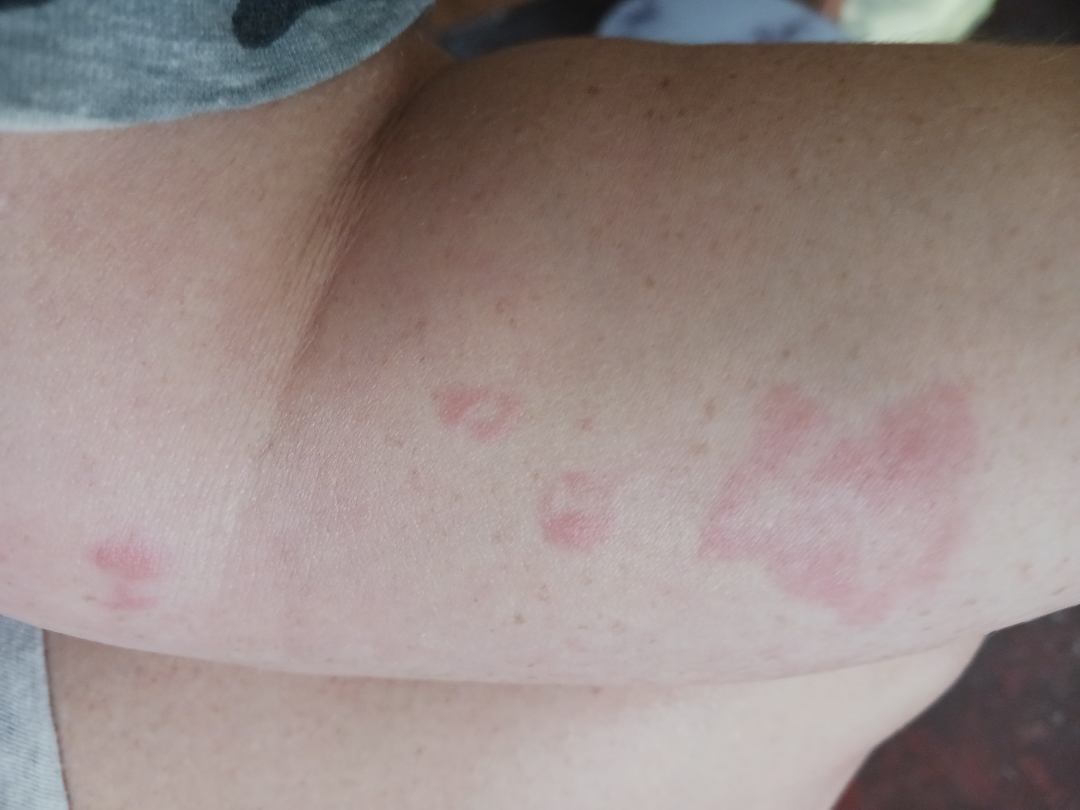Case summary:
– assessment: could not be assessed